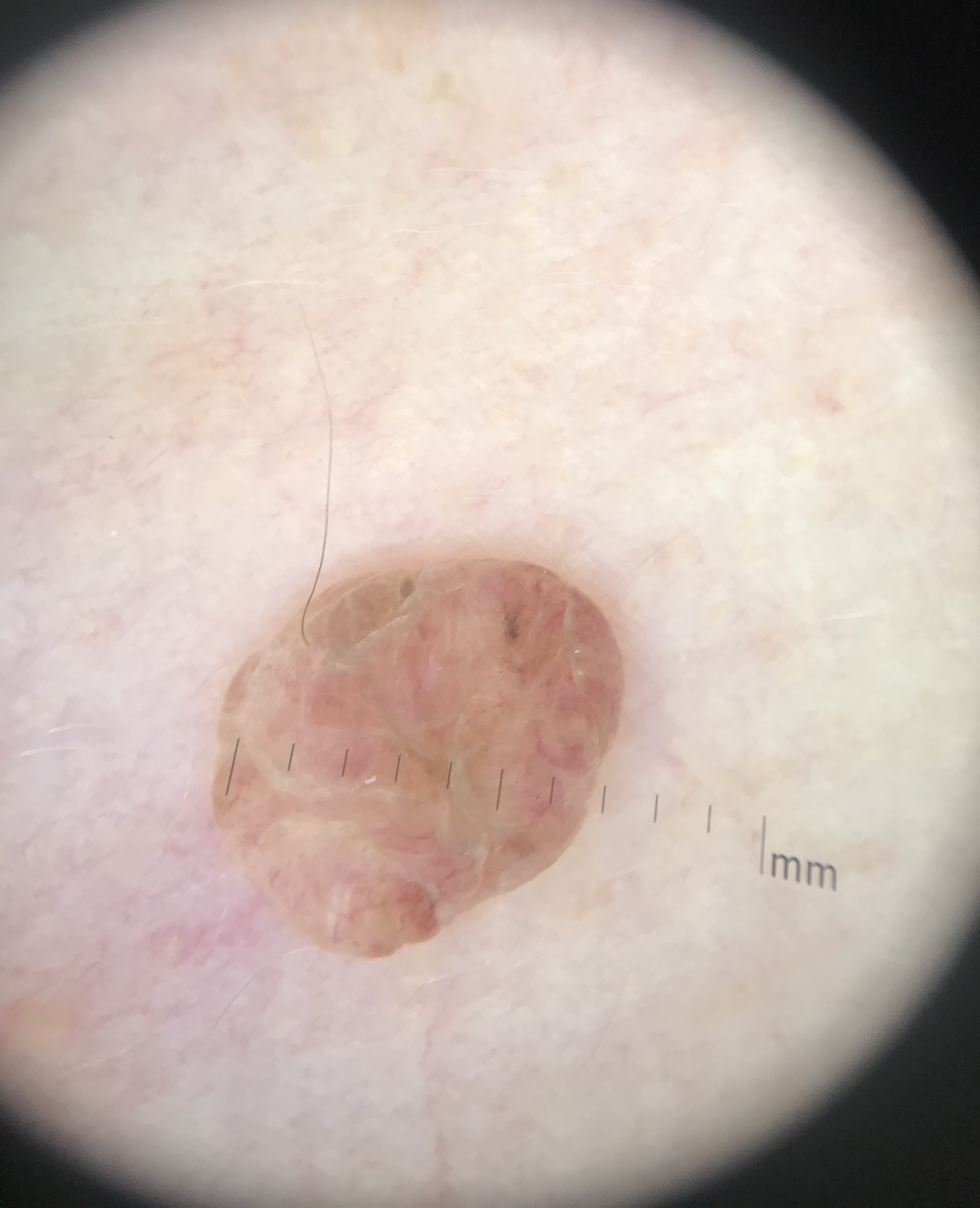modality = dermatoscopy | lesion type = banal | class = dermal nevus (expert consensus).